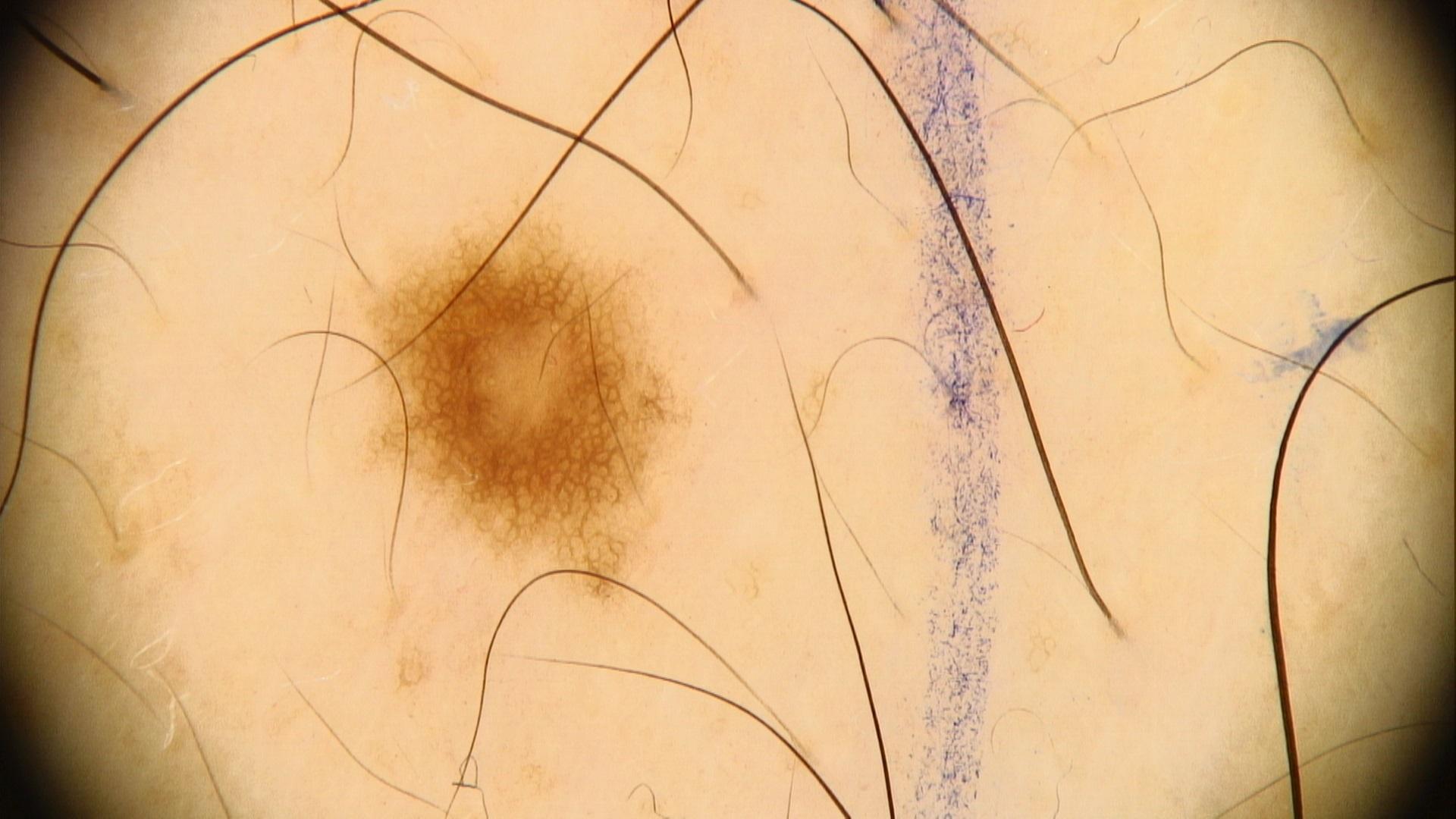{
  "image": "contact-polarized dermoscopy",
  "patient": {
    "age_approx": 40,
    "sex": "male"
  },
  "lesion_location": {
    "region": "the trunk"
  },
  "diagnosis": {
    "name": "Nevus",
    "malignancy": "benign",
    "confirmation": "expert clinical impression",
    "lineage": "melanocytic"
  }
}